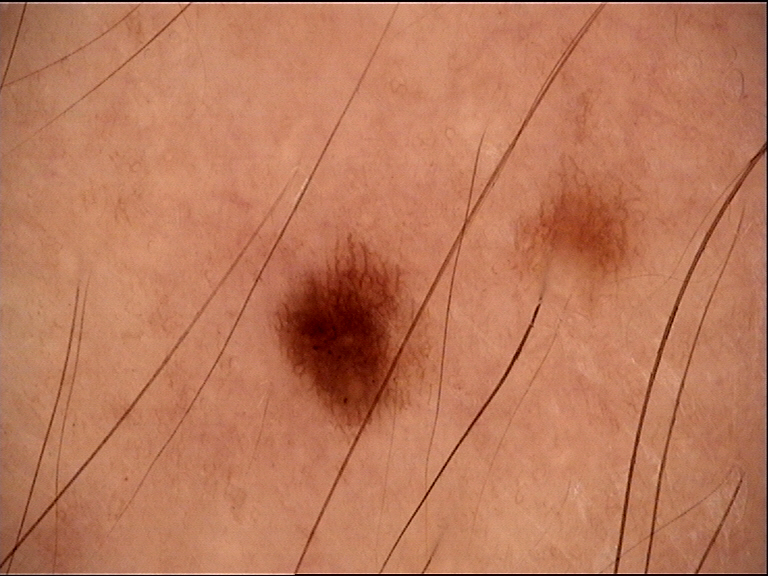A dermoscopic image of a skin lesion.
The diagnostic label was a dysplastic junctional nevus.